Located on the arm; the contributor is 40–49, female; the photograph is a close-up of the affected area:
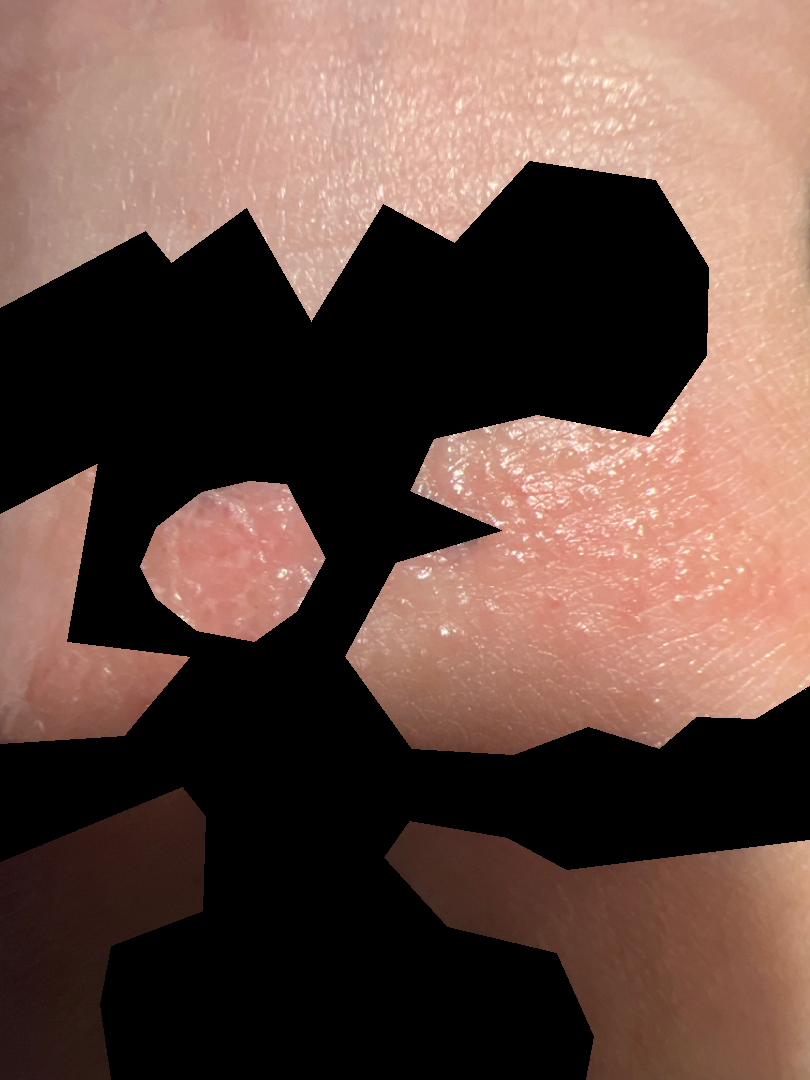Background: The contributor notes the lesion is fluid-filled and raised or bumpy. The patient described the issue as a rash. Reported lesion symptoms include enlargement, itching, burning and bothersome appearance. Present for one to four weeks. Findings: Three dermatologists independently reviewed the case: the leading consideration is Allergic Contact Dermatitis; also consider Herpes Zoster; lower on the differential is Impetigo.